Located on the leg. The photograph is a close-up of the affected area.
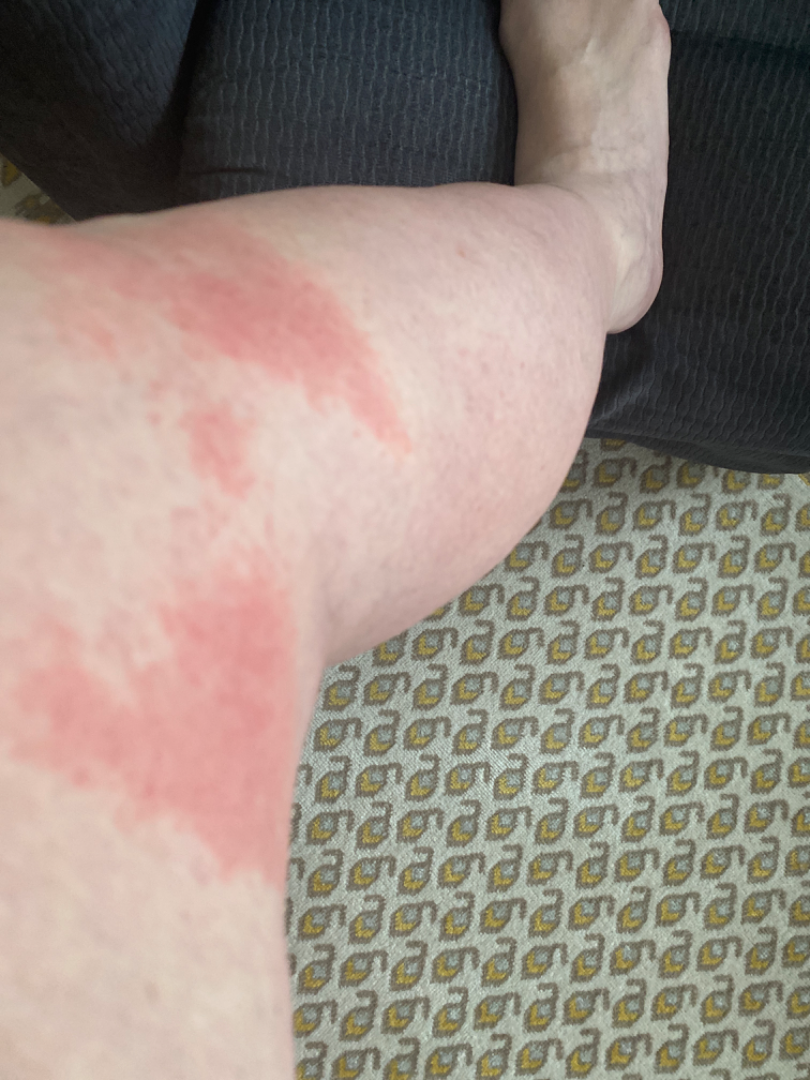Findings: A single dermatologist reviewed the case: the primary impression is Hypersensitivity; possibly Urticaria; an alternative is Eczema.